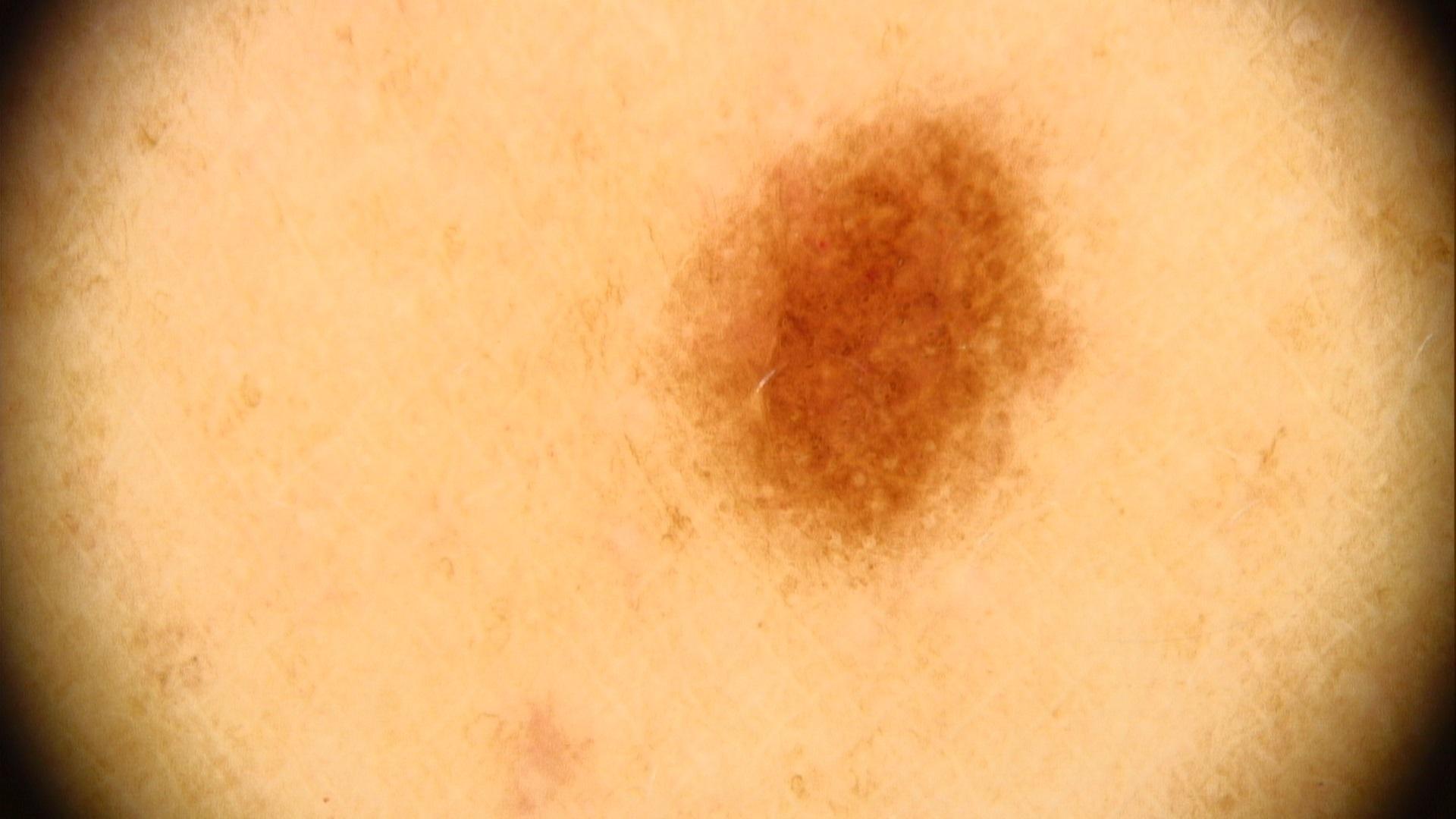Q: What is the anatomic site?
A: the trunk, specifically the posterior trunk
Q: What is this lesion?
A: Nevus